Female subject, age 40–49. The patient reported no systemic symptoms. Fitzpatrick phototype I; human graders estimated 2 on the Monk skin tone scale. Located on the leg. Present for less than one week. The photo was captured at a distance: 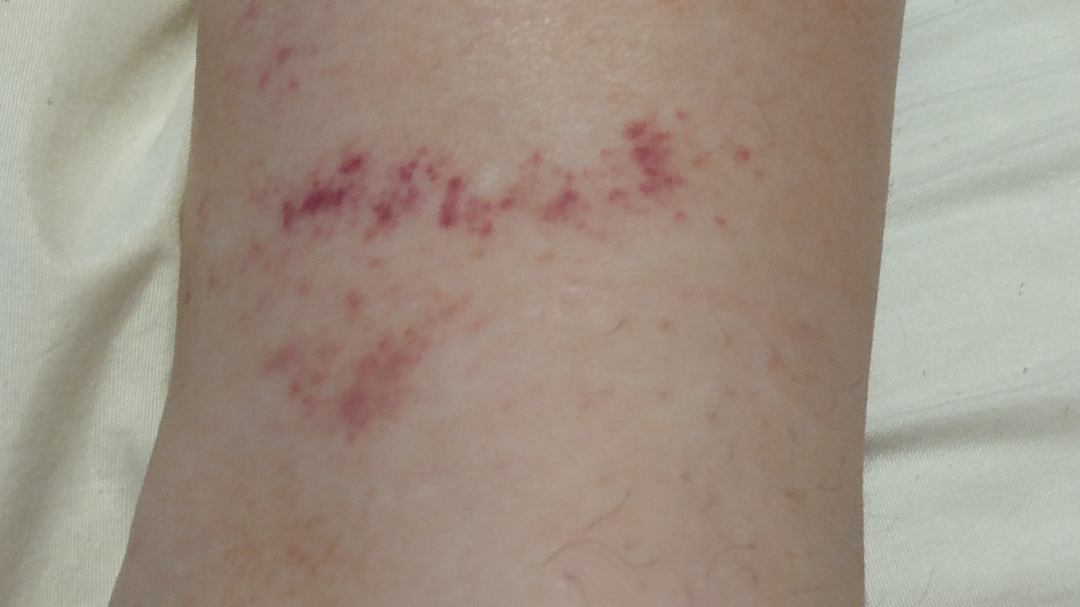Assessment: On photographic review, Pigmented purpuric eruption and Vasculitis of the skin were each considered, in no particular order.